The patient was assessed as Fitzpatrick II · the chart notes no melanoma in first-degree relatives and no prior melanoma.
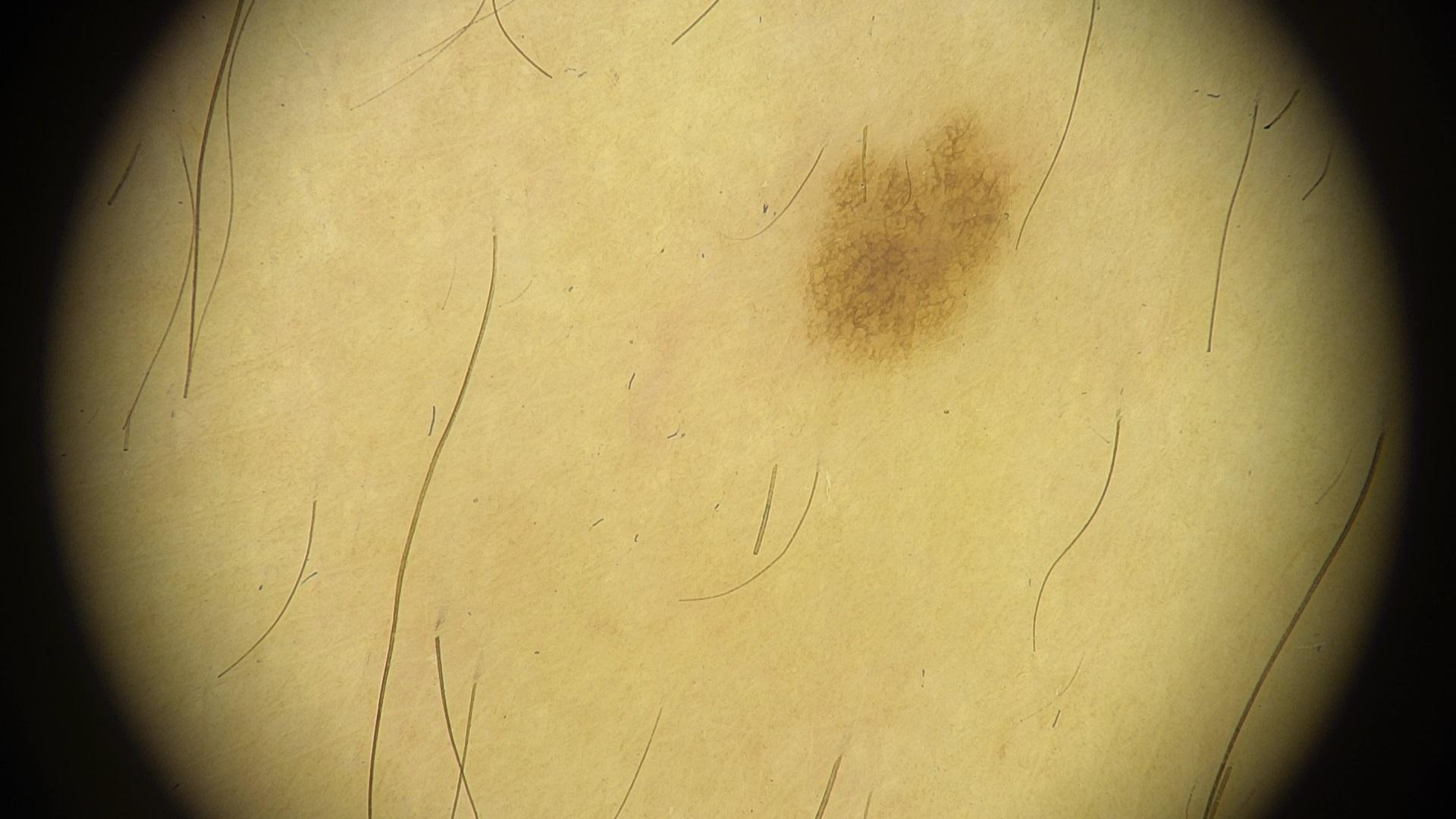The lesion is on the trunk. Expert review favored a nevus.